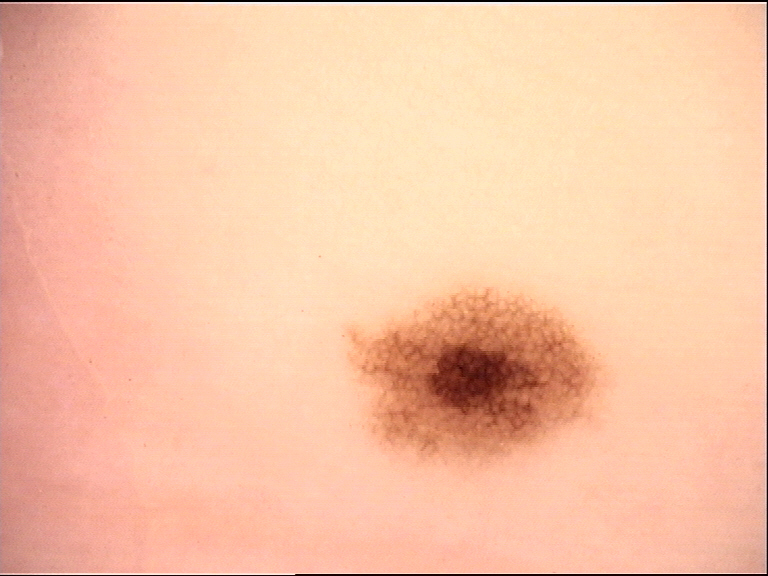A dermoscopic image of a skin lesion. Labeled as a dysplastic junctional nevus.